A dermoscopy image of a single skin lesion.
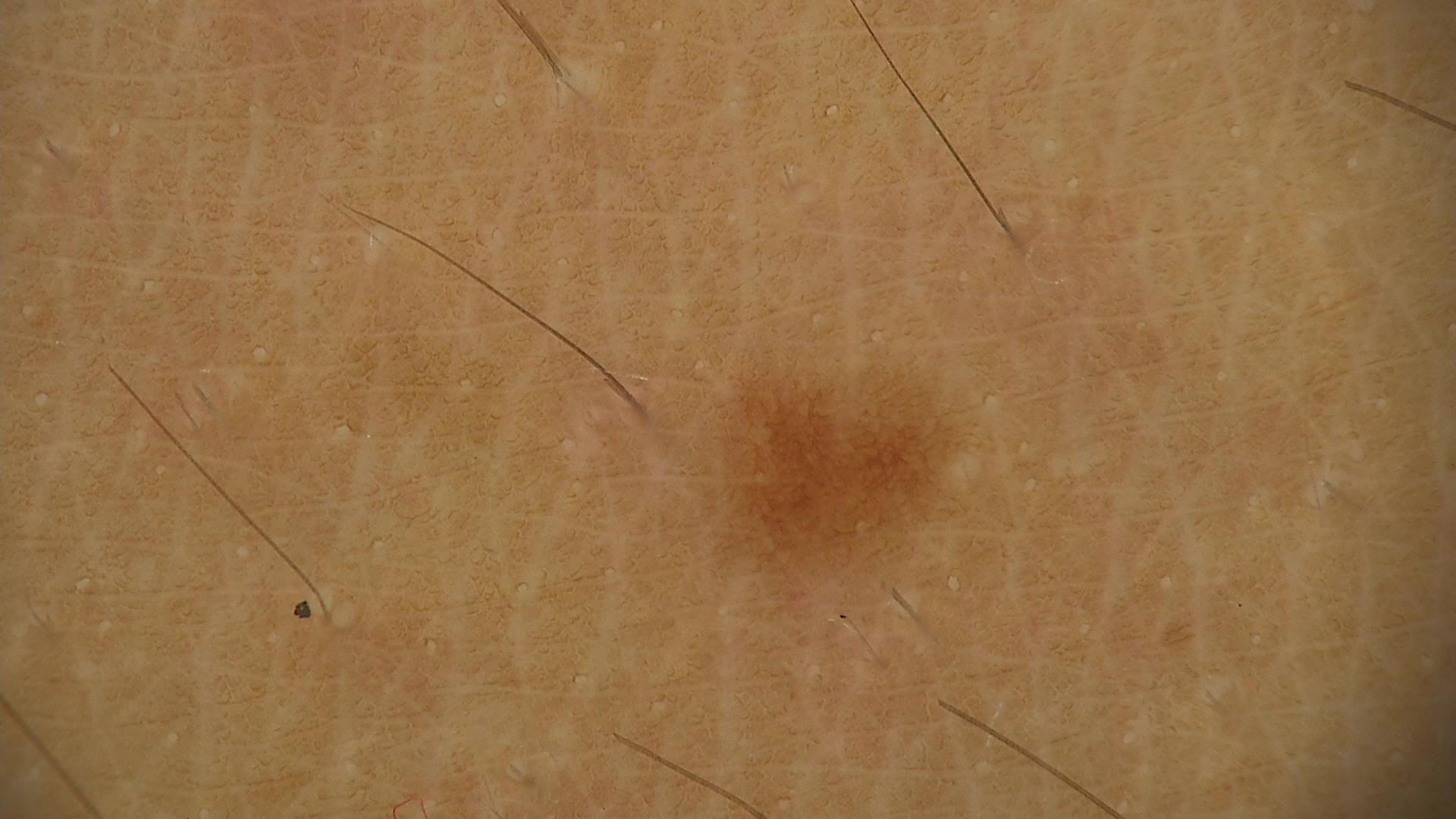Case:
* label · junctional nevus (expert consensus)